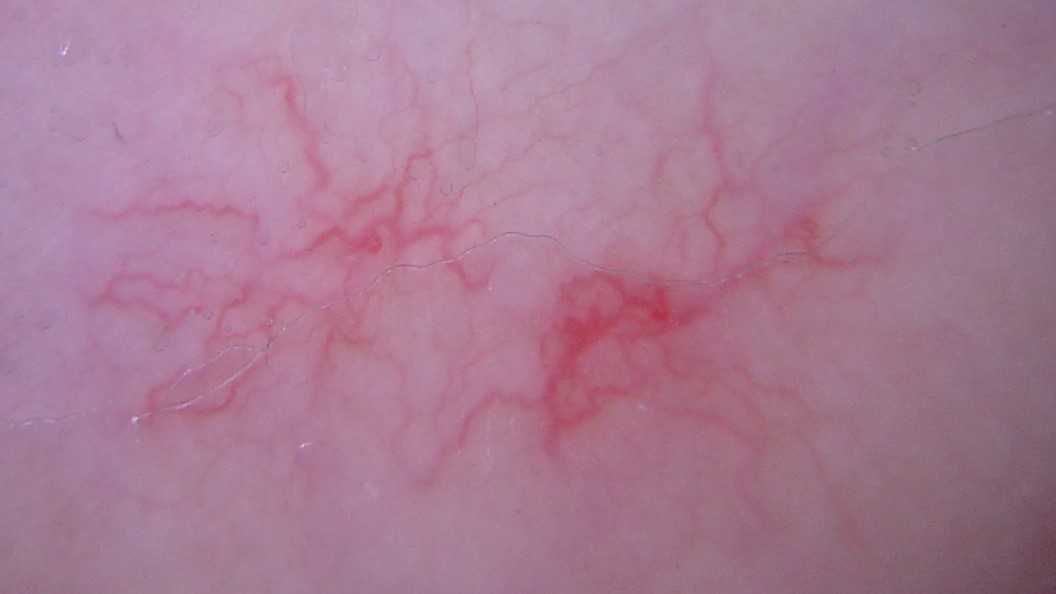  diagnosis:
    name: spider angioma
    code: sa
    malignancy: benign
    super_class: non-melanocytic
    confirmation: expert consensus